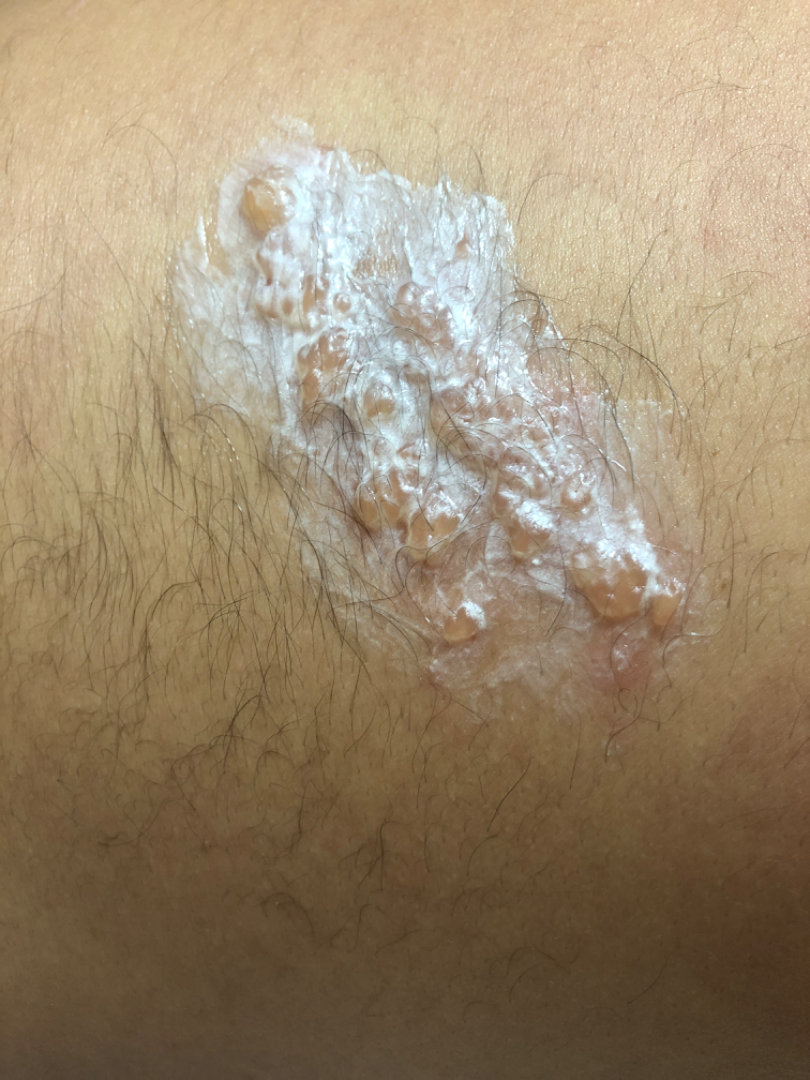differential = single-reviewer assessment: favoring Herpes Simplex; also consider Herpes Zoster.